The affected area is the arm; the photograph is a close-up of the affected area — 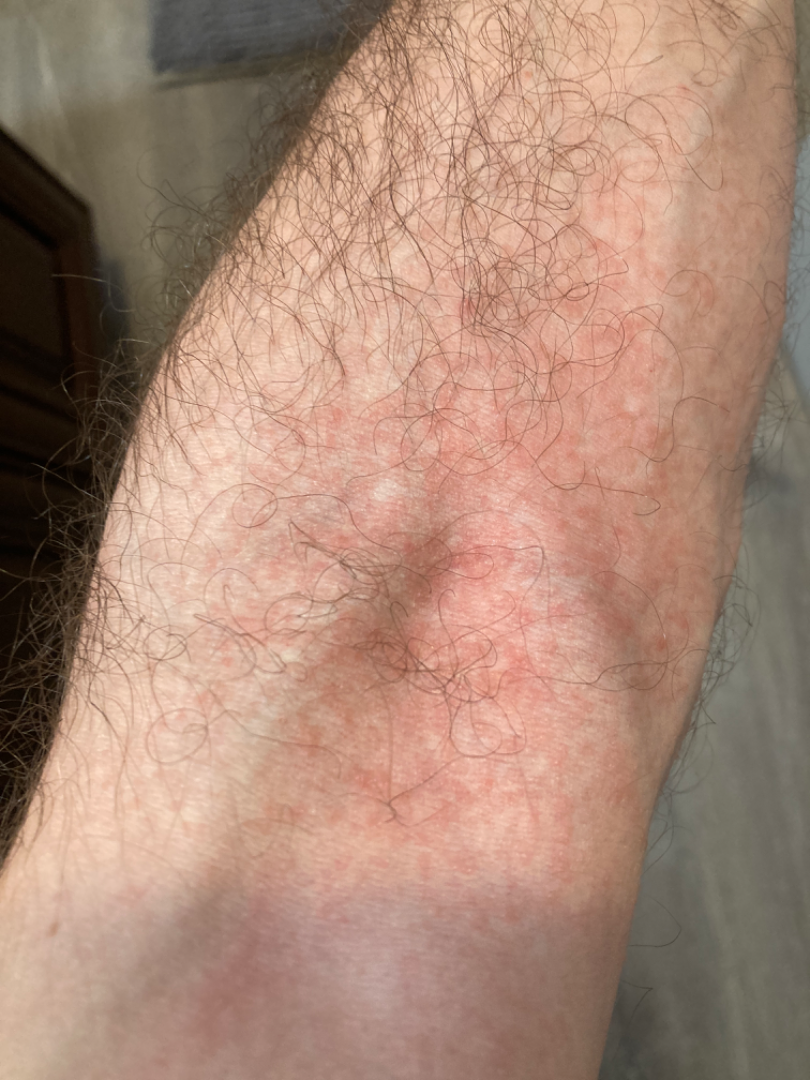reported symptoms: itching; associated systemic symptoms: none reported; duration: less than one week; texture: raised or bumpy; dermatologist impression: the differential includes Hypersensitivity and Allergic Contact Dermatitis, with no clear leading consideration.